Close-up view: 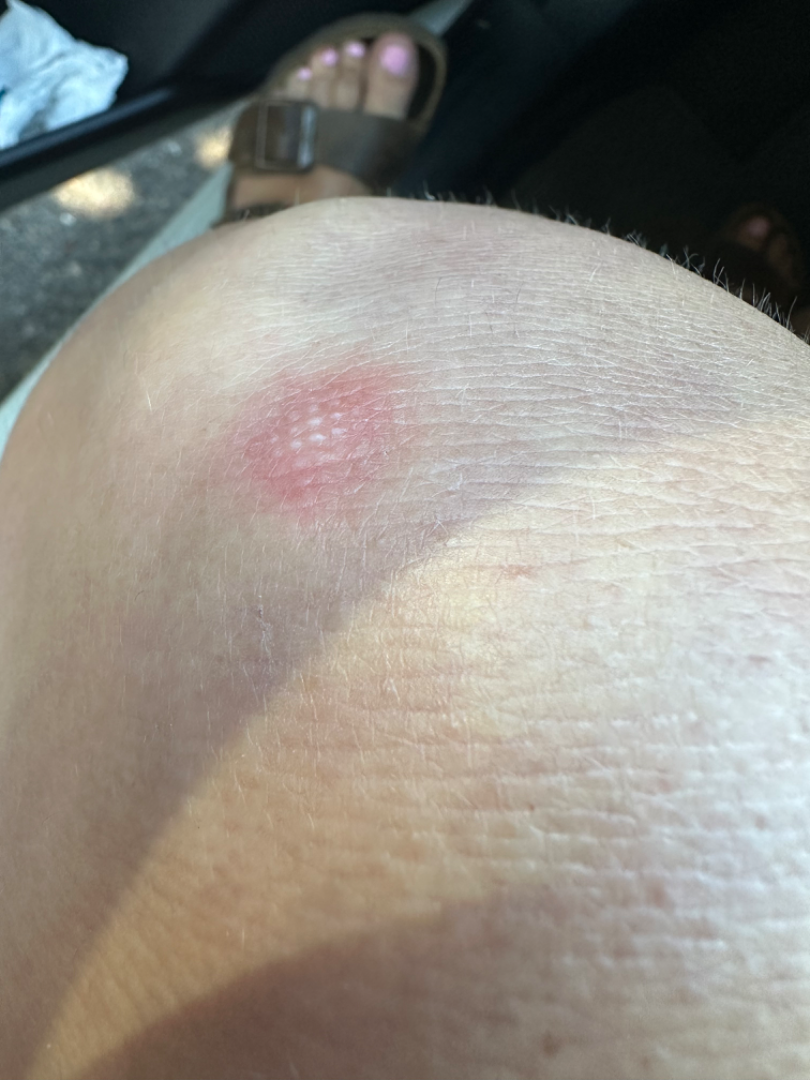Findings: The reviewer was unable to grade this case for skin condition.